A skin lesion imaged with a dermatoscope.
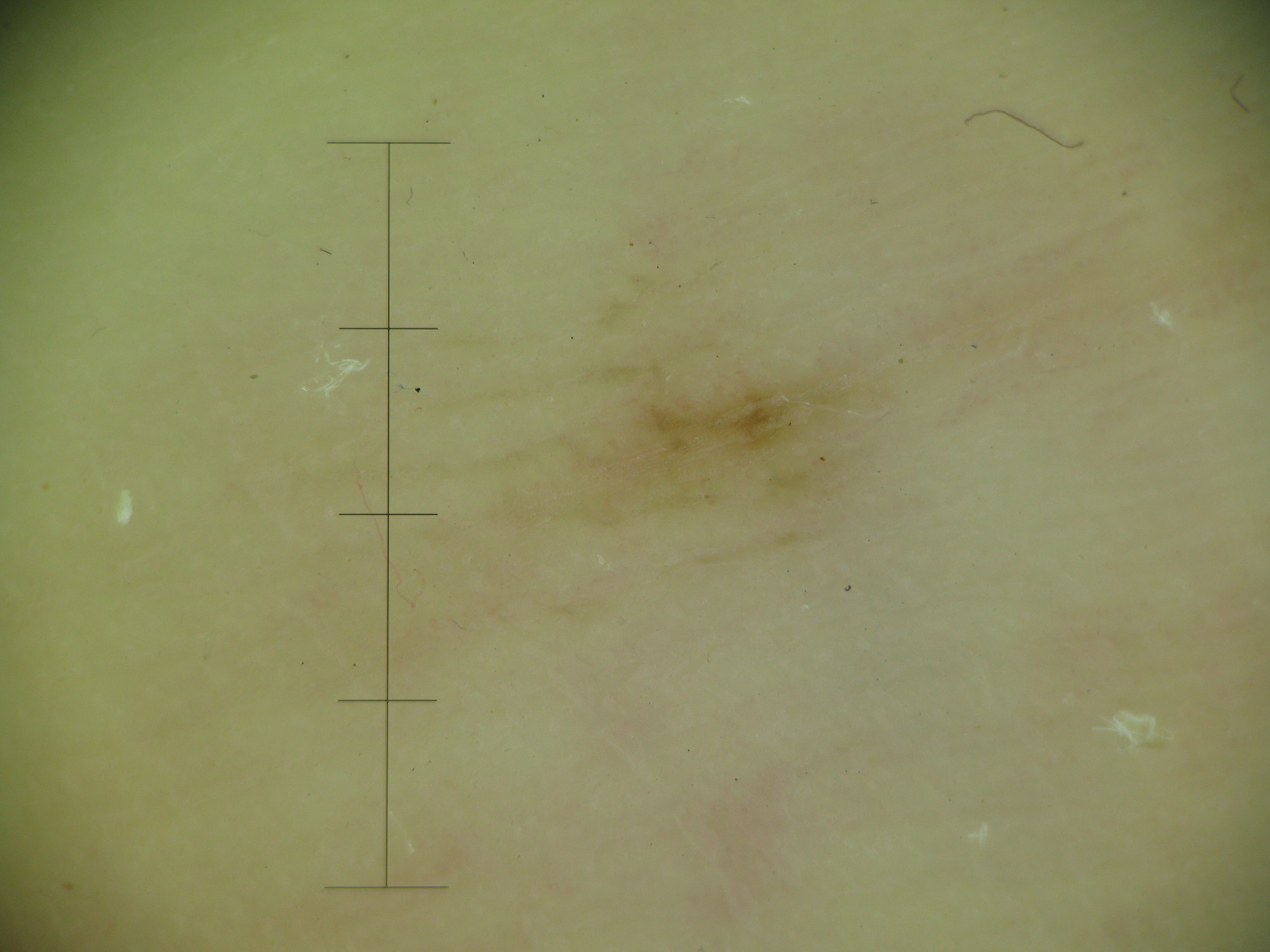Classified as an acral dysplastic junctional nevus.